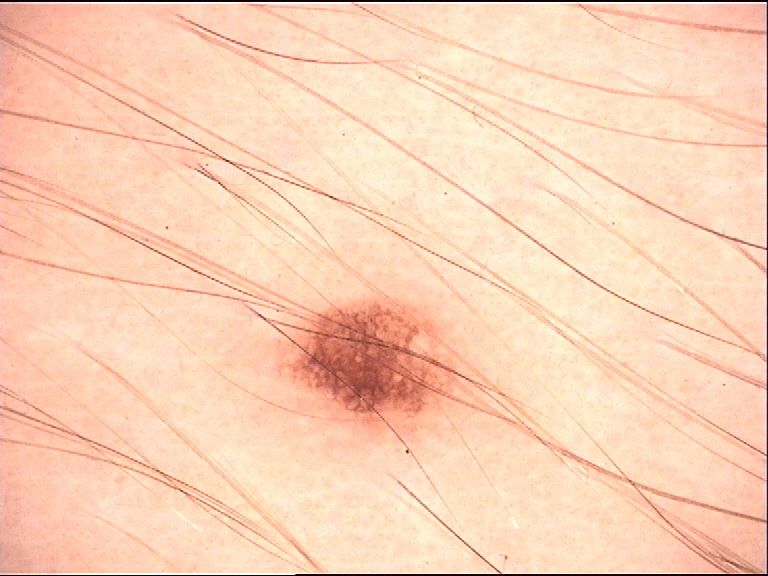The diagnostic label was a junctional nevus.